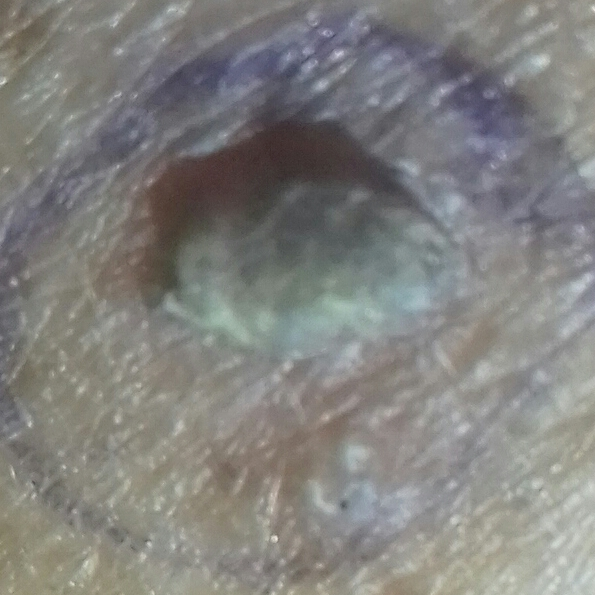The lesion is located on an arm. By the patient's account, the lesion is elevated, but has not changed. Histopathologically confirmed as an actinic keratosis.